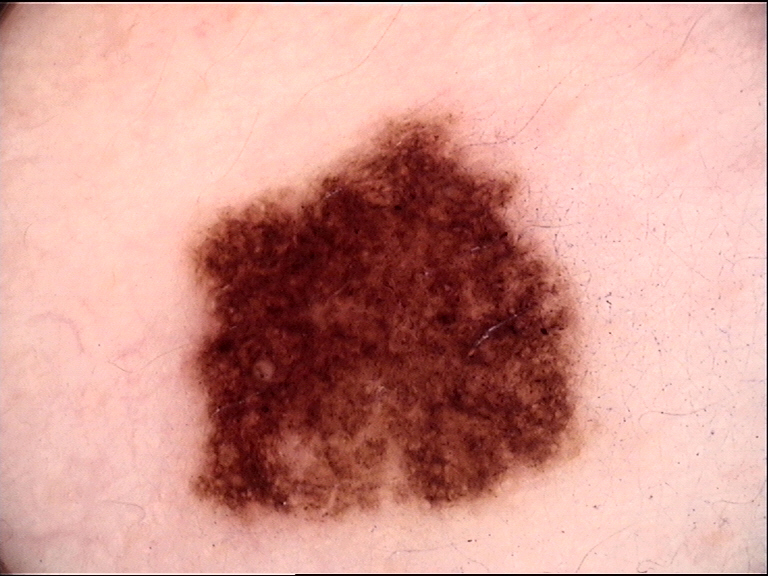Q: What was the diagnostic impression?
A: dysplastic compound nevus (expert consensus)